The patient reported no systemic symptoms. The lesion involves the arm. Texture is reported as raised or bumpy. Symptoms reported: enlargement, bothersome appearance and itching. An image taken at an angle — 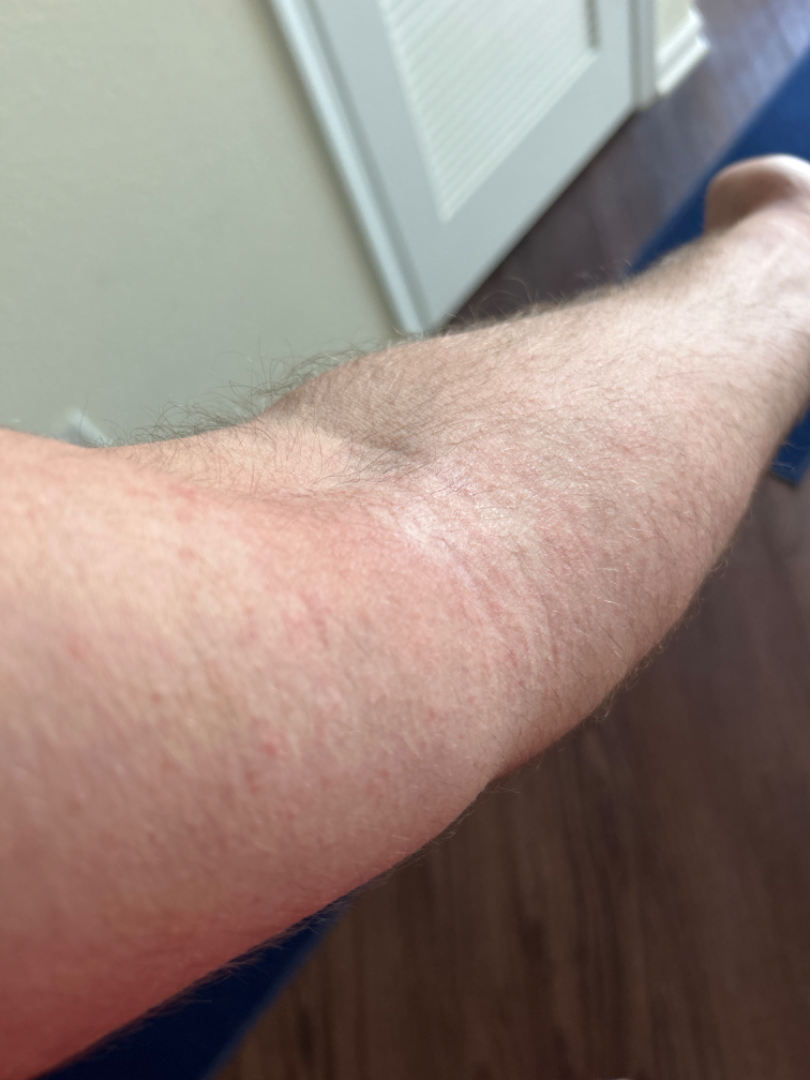Impression: On remote dermatologist review, Eczema (primary); Contact dermatitis, NOS (possible); Viral Exanthem (less likely).